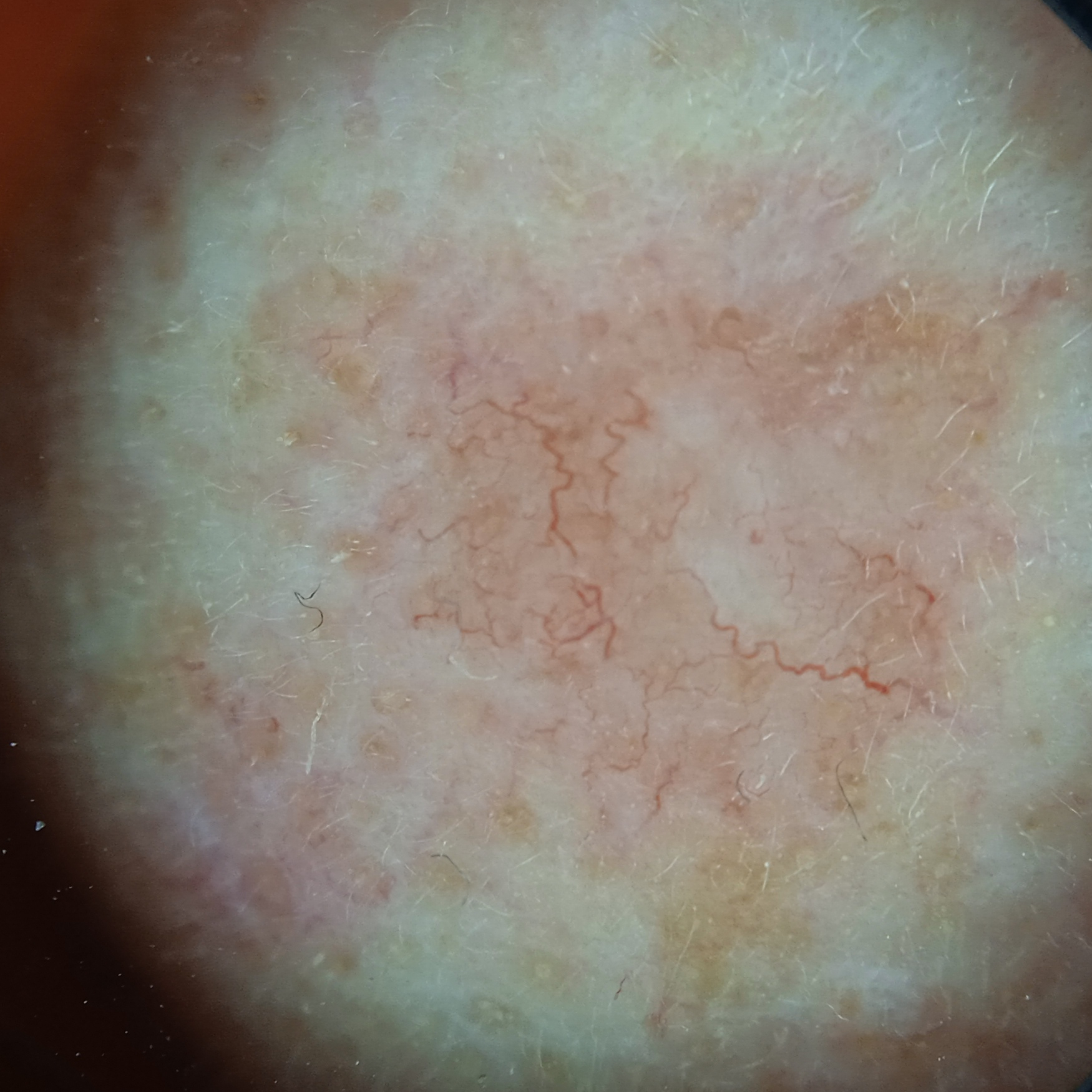  image: dermoscopic image
  mole_burden: few melanocytic nevi overall
  risk_factors:
    positive:
      - a personal history of cancer
  referral: clinical suspicion of basal cell carcinoma
  sun_reaction: skin tans without first burning
  lesion_location: the face
  diagnosis:
    name: basal cell carcinoma
    malignancy: malignant
    procedure: excision
    tumor_thickness_mm: 1.5